The chart notes prior skin cancer (patient or family) and pesticide exposure · a clinical close-up photograph of a skin lesion.
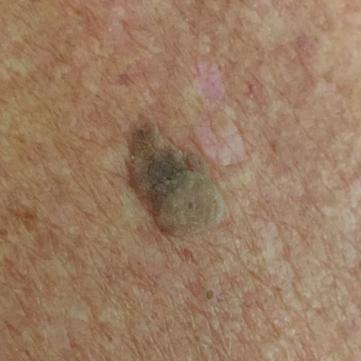Patient and lesion:
The lesion involves the back. The lesion is roughly 10 by 8 mm. By the patient's account, the lesion is elevated, itches, and has grown, but has not bled.
Conclusion:
The consensus clinical diagnosis was a seborrheic keratosis.